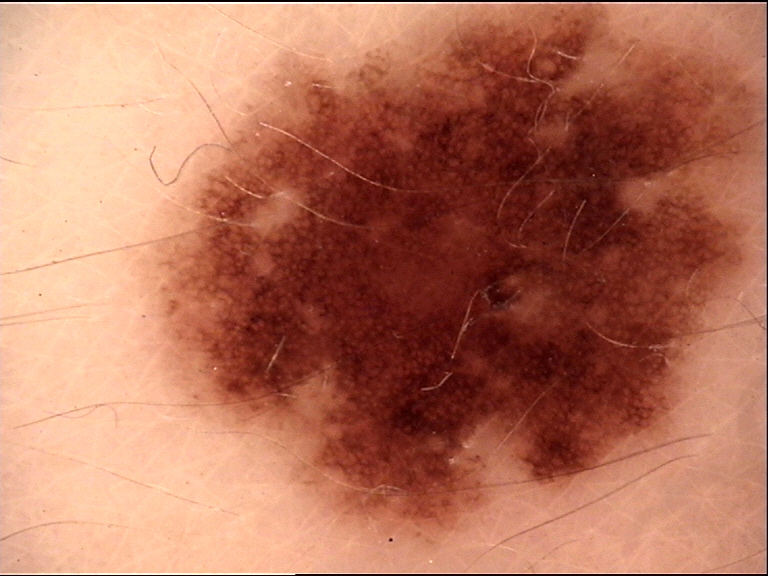A dermoscopy image of a single skin lesion.
The diagnostic label was a dysplastic junctional nevus.